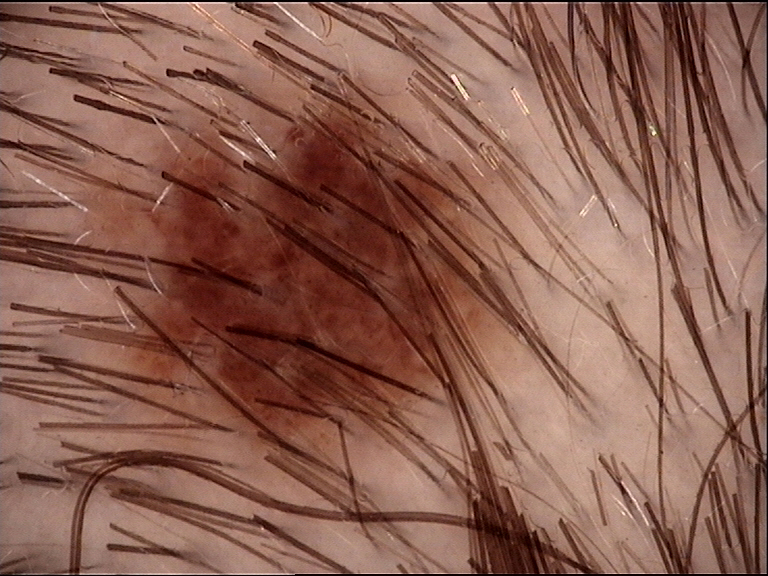Labeled as a dysplastic junctional nevus.